Dermoscopy of a skin lesion.
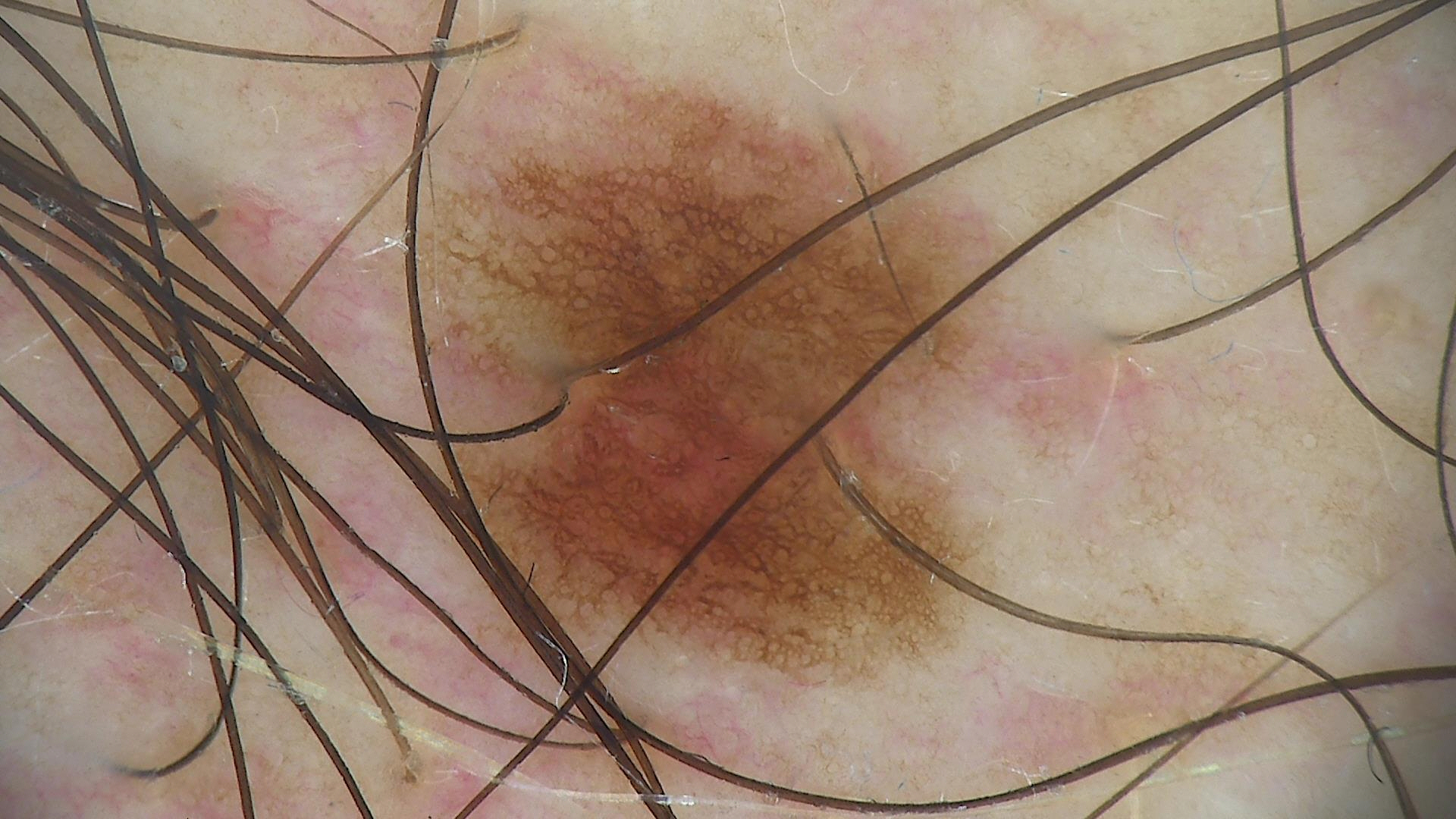<dermoscopy>
<diagnosis>
<name>dysplastic junctional nevus</name>
<code>jd</code>
<malignancy>benign</malignancy>
<super_class>melanocytic</super_class>
<confirmation>expert consensus</confirmation>
</diagnosis>
</dermoscopy>